A female subject 59 years of age; a clinical close-up photograph of a skin lesion; by history, prior malignancy (patient or family) and prior skin cancer (patient or family).
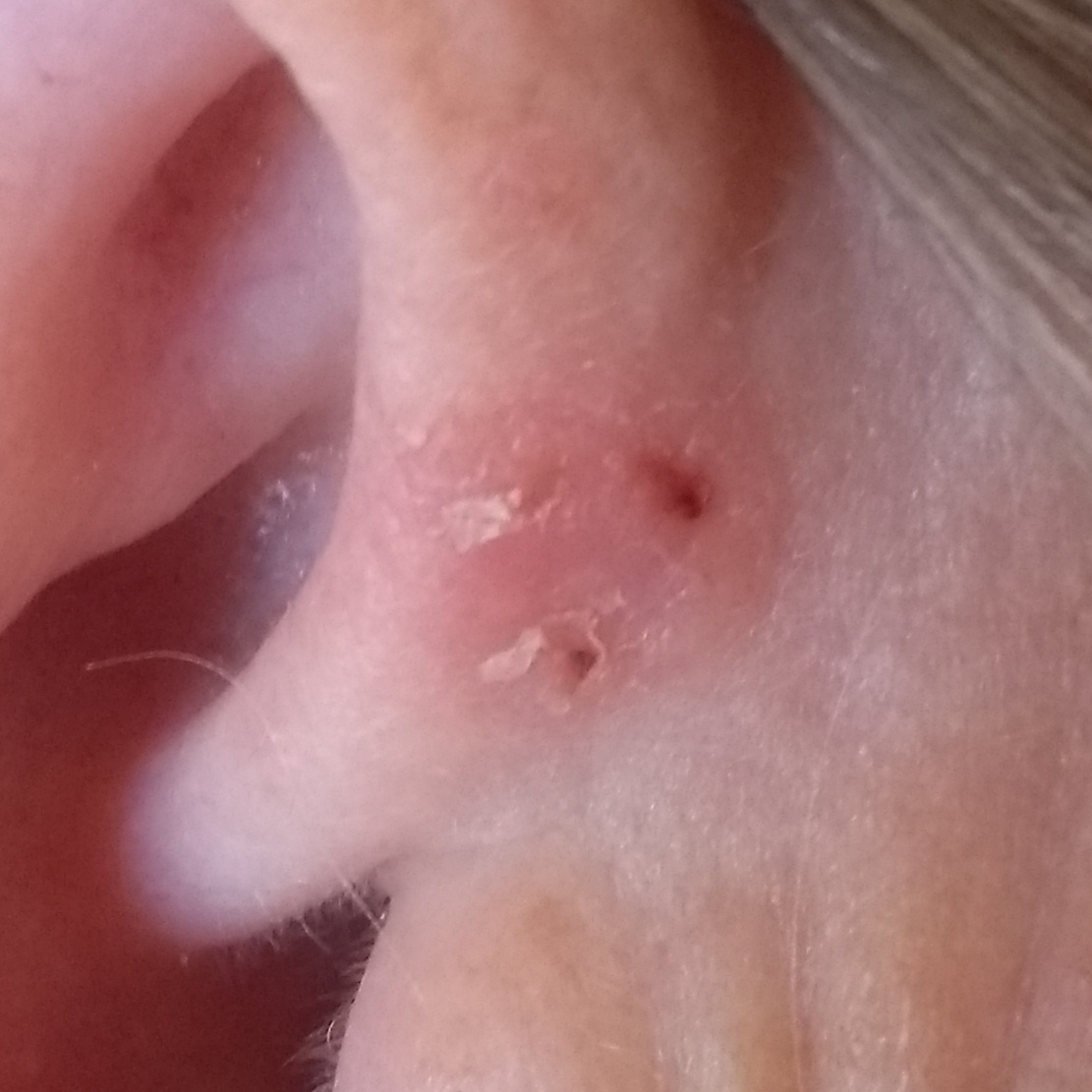Summary: Measuring about 7 × 6 mm. Conclusion: The biopsy diagnosis was a basal cell carcinoma.